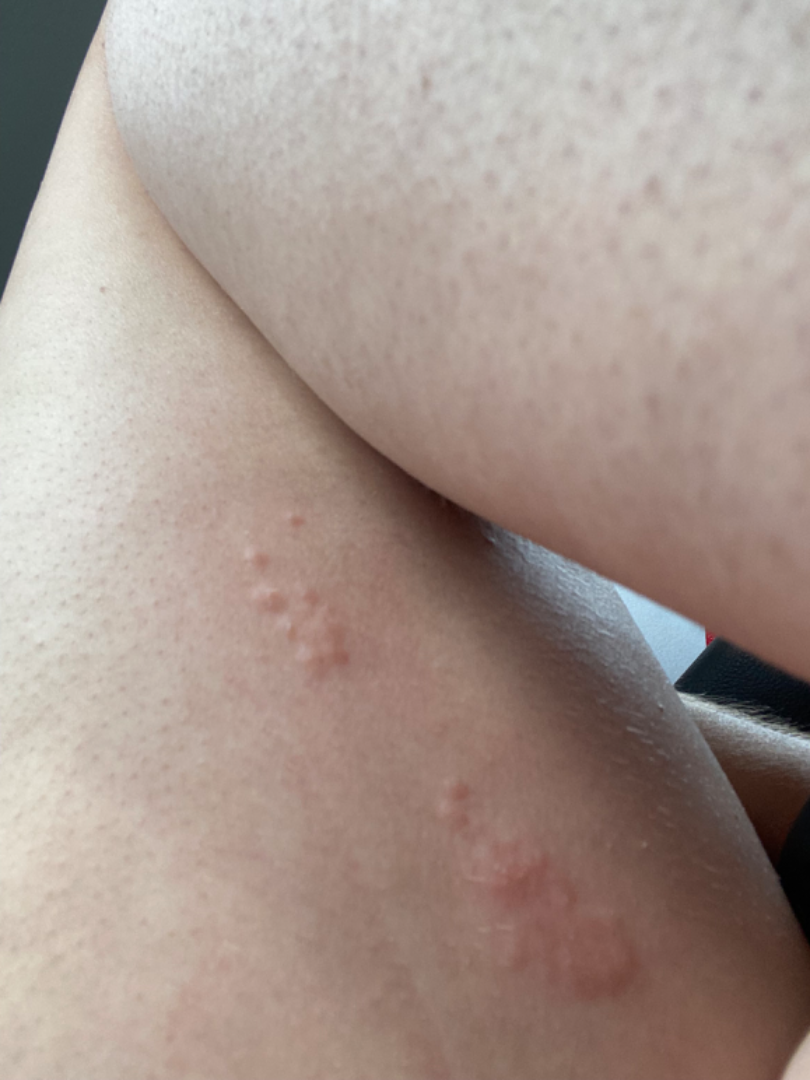The case was difficult to assess from the available photograph. This image was taken at an angle.